Located on the leg. A close-up photograph. The subject is 18–29, female: 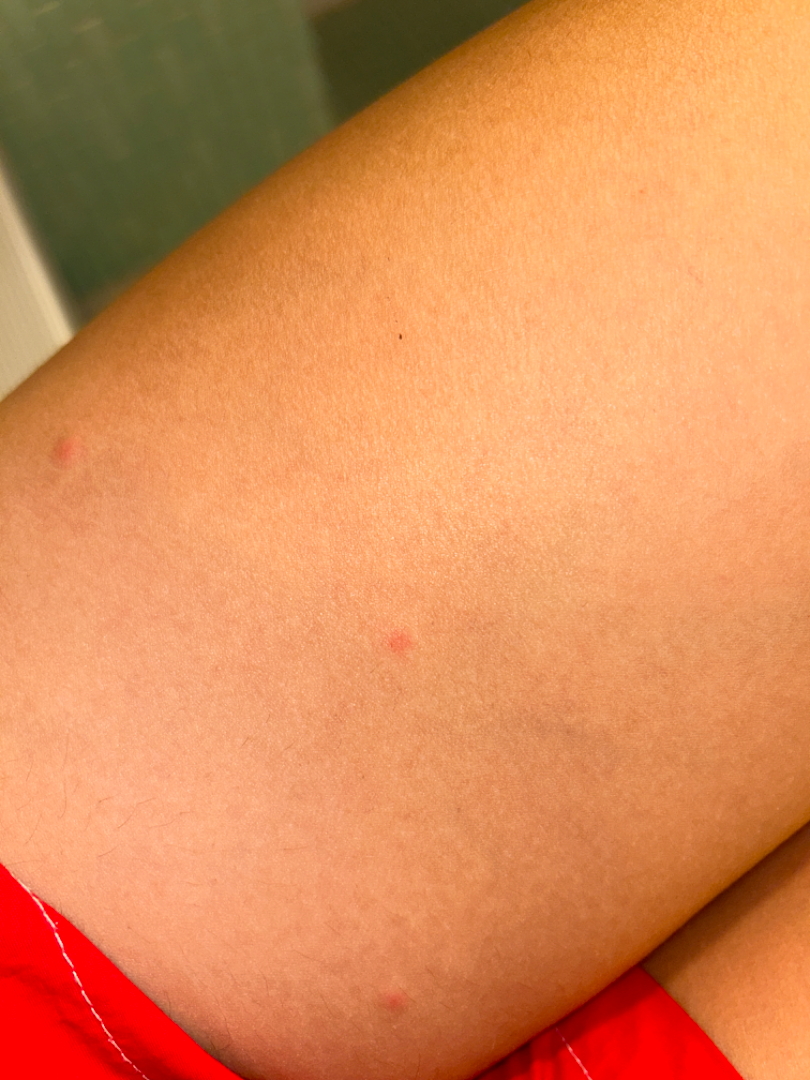Symptoms reported: bothersome appearance.
No constitutional symptoms were reported.
The patient notes the lesion is raised or bumpy.
Present for about one day.
On dermatologist assessment of the image, Insect Bite (favored); Folliculitis (possible).